Texture is reported as flat. The patient considered this a rash. The photograph was taken at a distance. The leg is involved. No associated systemic symptoms reported: 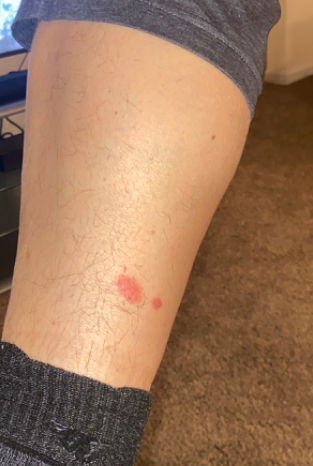Findings: Insect Bite (primary); Eczema (considered); Allergic Contact Dermatitis (considered).